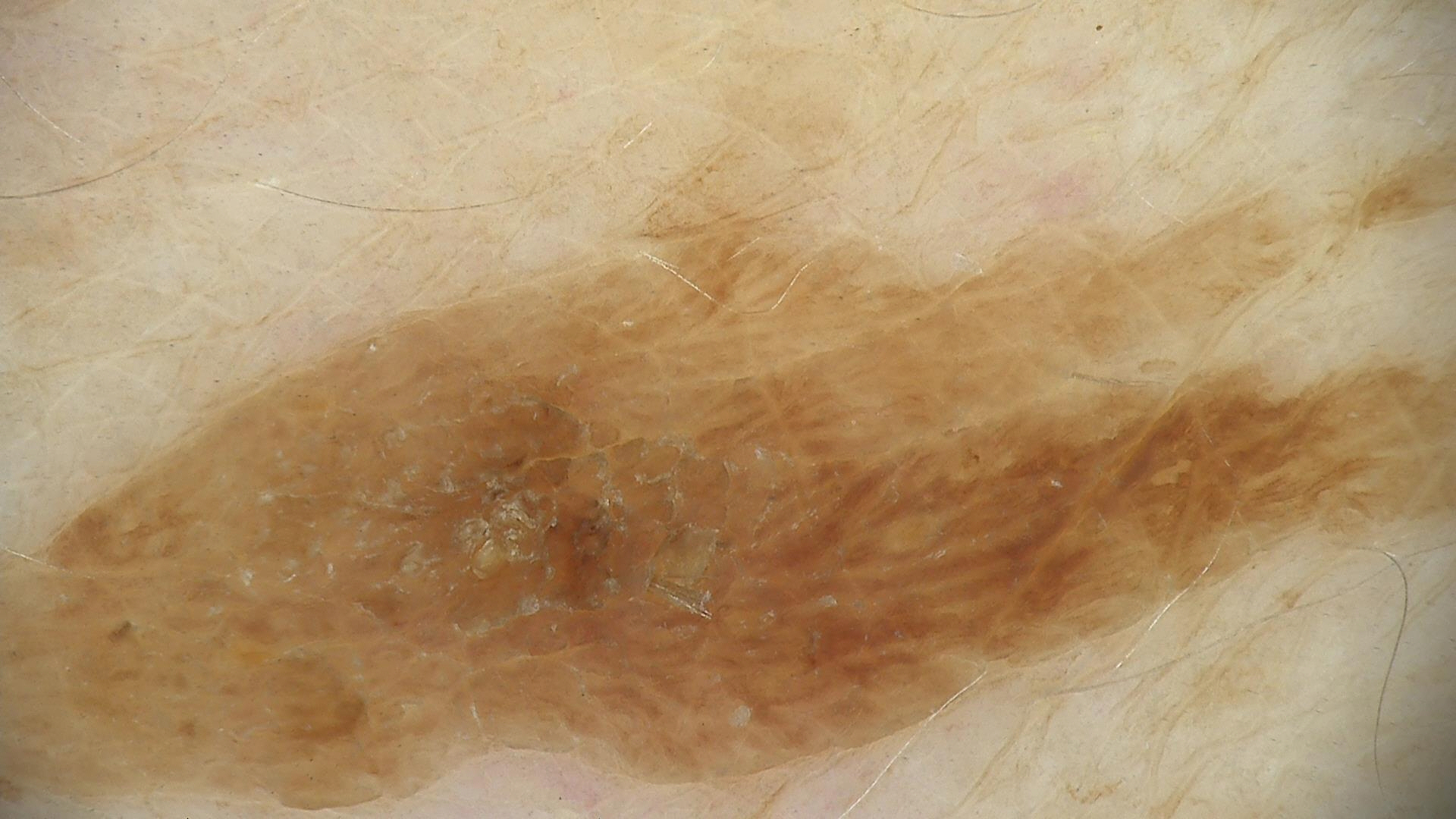A dermoscopic close-up of a skin lesion. The architecture is that of a keratinocytic lesion. The diagnosis was a benign lesion — a seborrheic keratosis.